The arm and leg are involved; this image was taken at an angle.
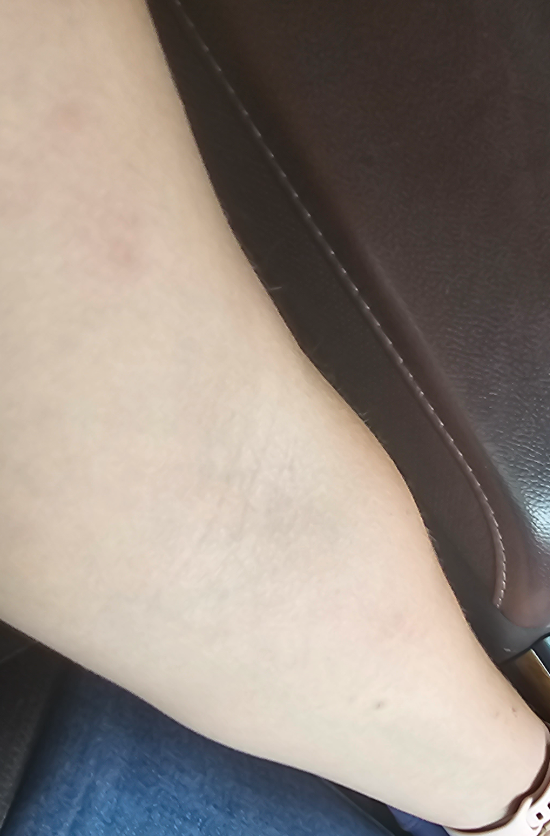The reviewing dermatologist was unable to assign a differential diagnosis from the image. Reported duration is one to four weeks. The patient notes the lesion is raised or bumpy and fluid-filled.